The lesion involves the leg. Female contributor, age 30–39. The photograph was taken at an angle: 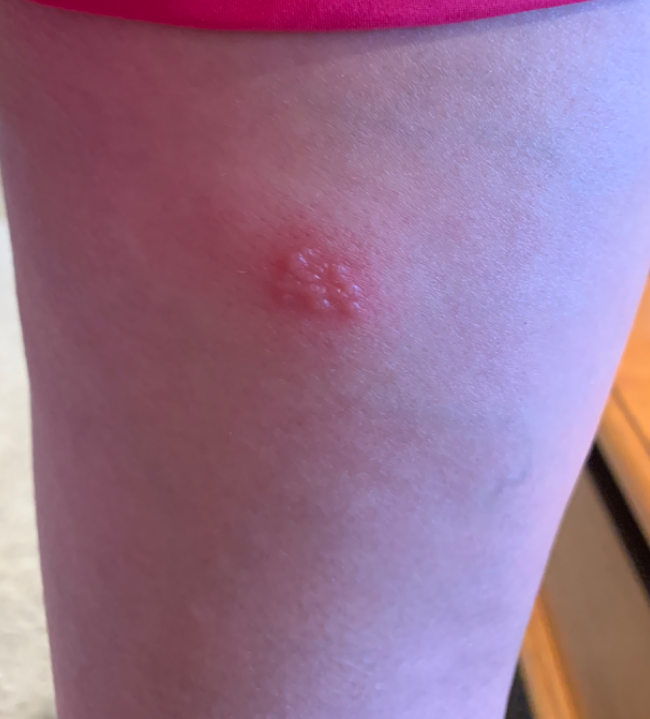The lesion is associated with bothersome appearance, pain, itching, burning and enlargement.
The condition has been present for less than one week.
The impression on review was Herpes Simplex.